A dermoscopy image of a single skin lesion: 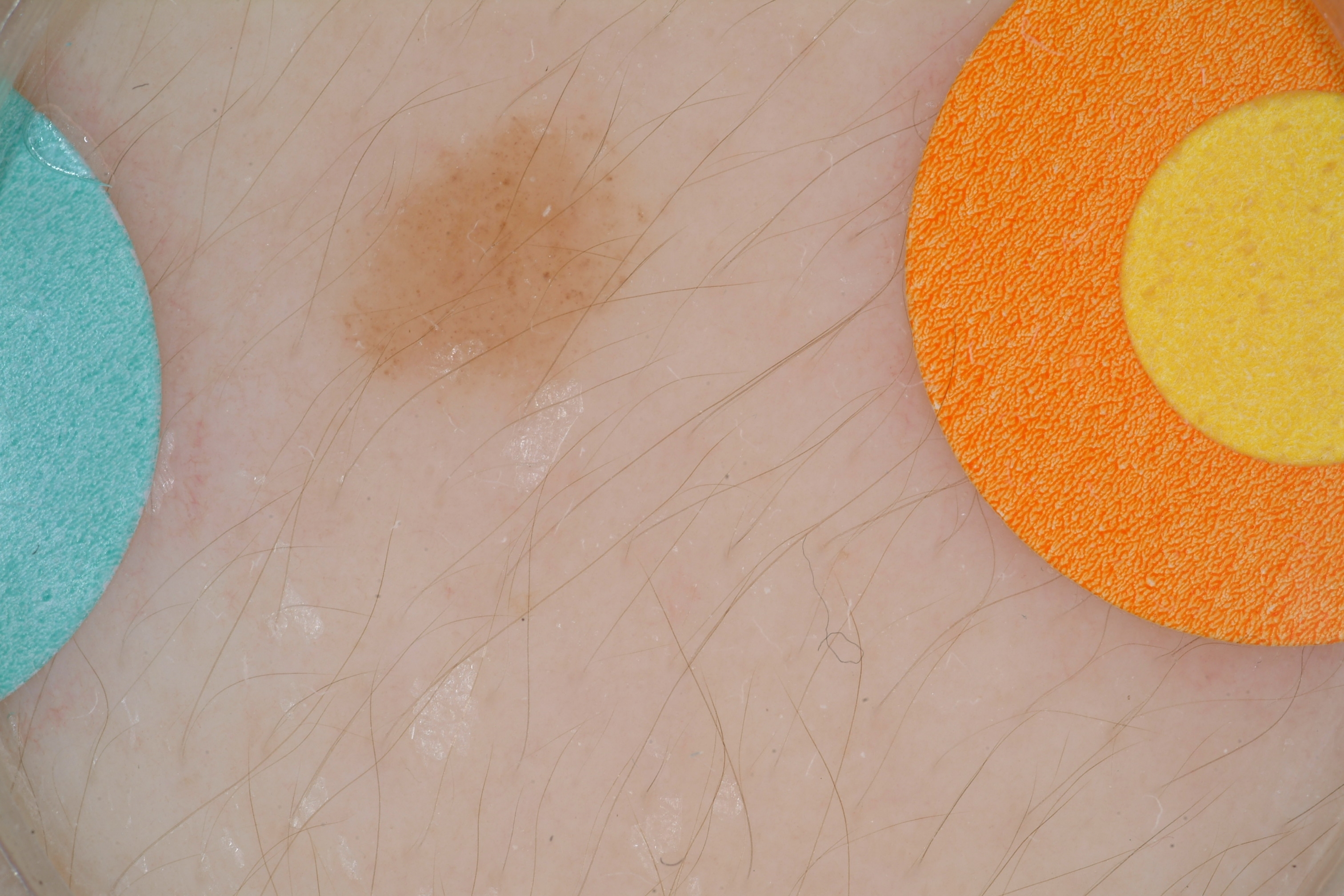location — 325, 80, 707, 427
dermoscopic findings — globules; absent: streaks
extent — small
impression — a benign skin lesion